The patient is Fitzpatrick phototype III; a female patient aged around 85 or older:
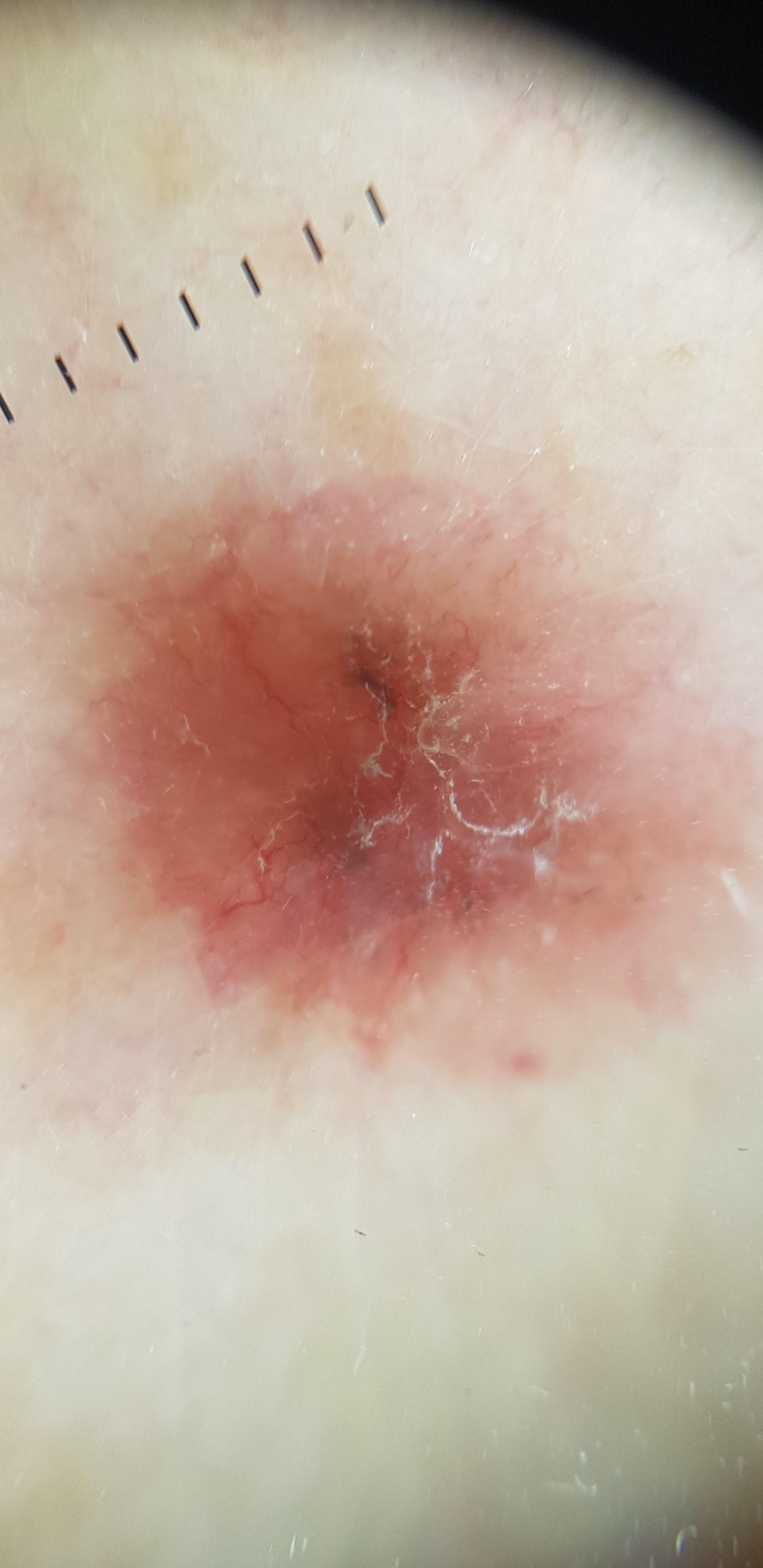diagnostic label: Basal cell carcinoma (biopsy-proven).